Dermoscopy of a skin lesion: 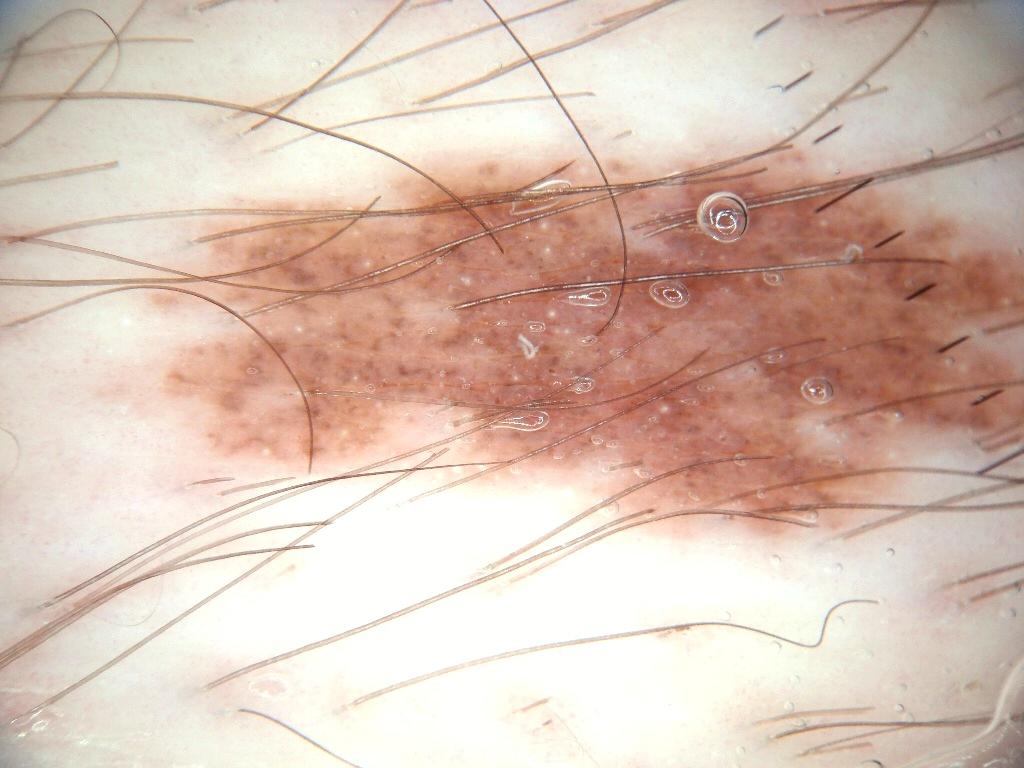Dermoscopic assessment notes milia-like cysts, with no negative network, globules, pigment network, or streaks.
The lesion takes up a large portion of the image.
The visible lesion spans x1=137 y1=141 x2=1022 y2=548.
Diagnosed as a melanocytic nevus.